A dermoscopic view of a skin lesion; a female patient, aged around 40 — 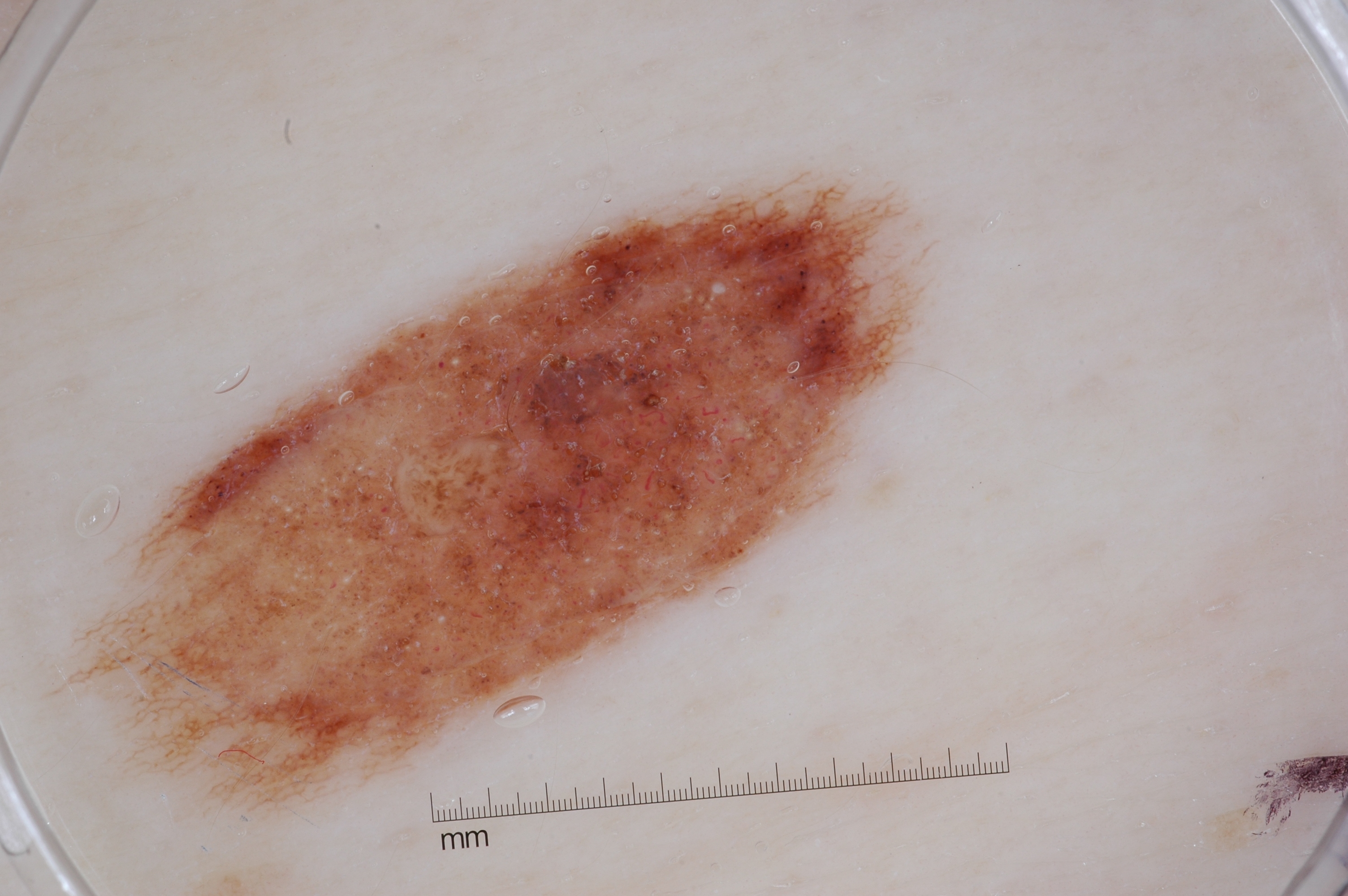On dermoscopy, the lesion shows milia-like cysts and pigment network, with no negative network or streaks. With coordinates (x1, y1, x2, y2), lesion location: box(106, 189, 906, 805). Diagnosed as a melanocytic nevus, a benign skin lesion.